Texture is reported as raised or bumpy · no associated systemic symptoms reported · the patient indicates the condition has been present for one to four weeks · the photograph is a close-up of the affected area · the affected area is the top or side of the foot — 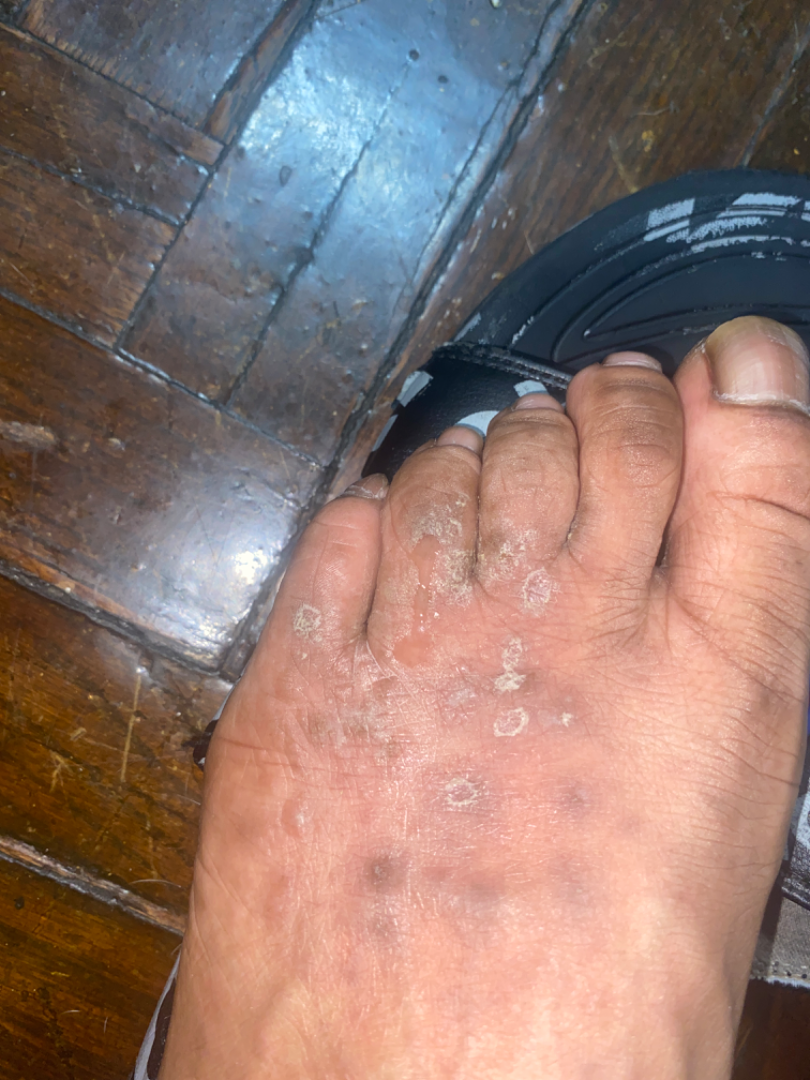Q: What is the differential diagnosis?
A: Drug Rash (considered); Psoriasiform dermatitis (considered)